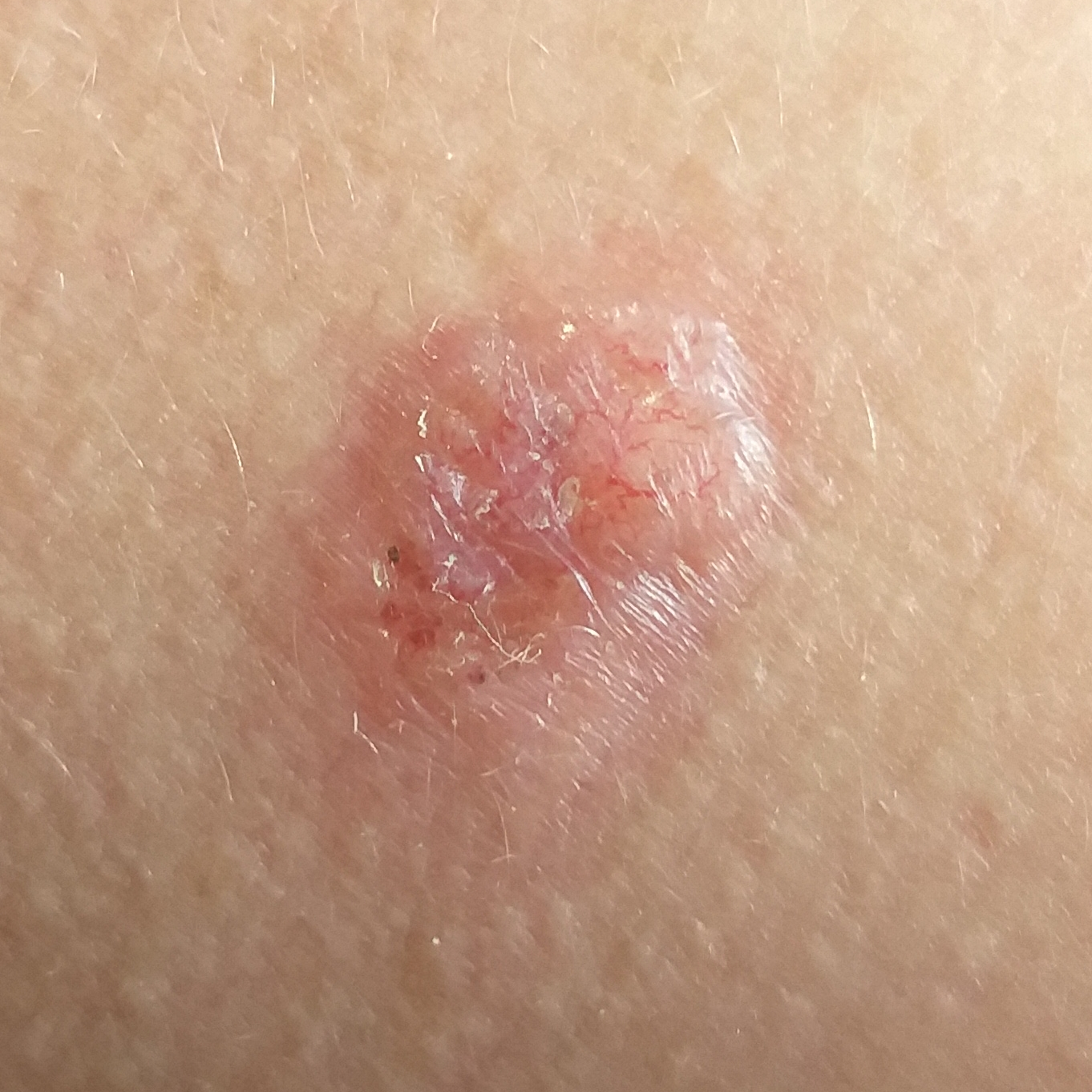Conclusion:
Histopathological examination showed a basal cell carcinoma.